A male subject aged 68-72. A dermoscopy image of a single skin lesion — 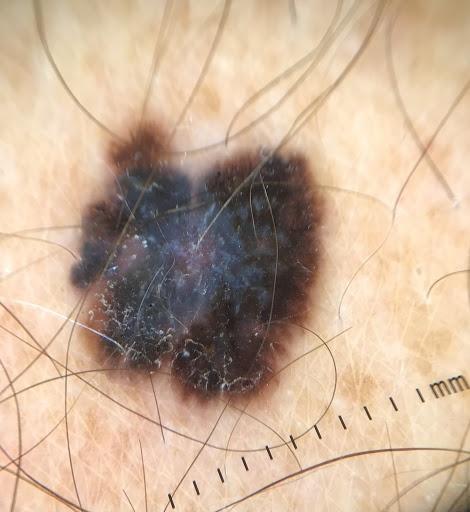The biopsy diagnosis was a malignancy — a melanoma.